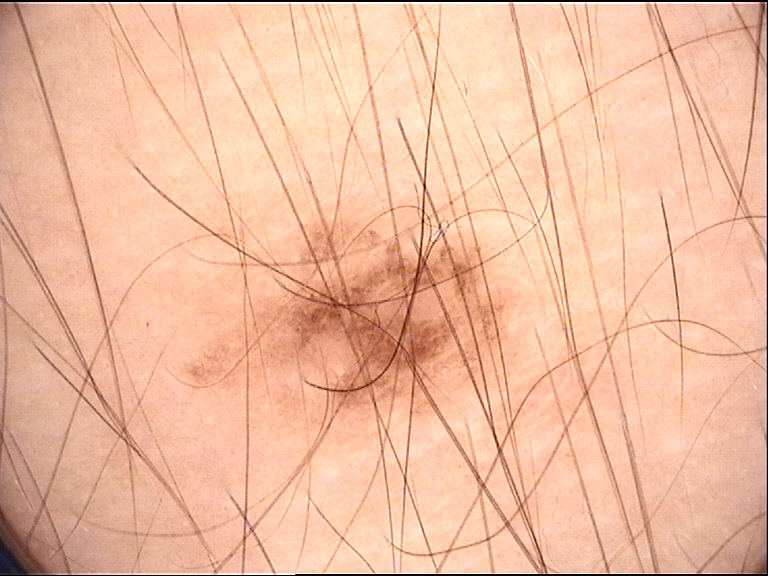image — dermatoscopy | diagnosis — junctional nevus (expert consensus).